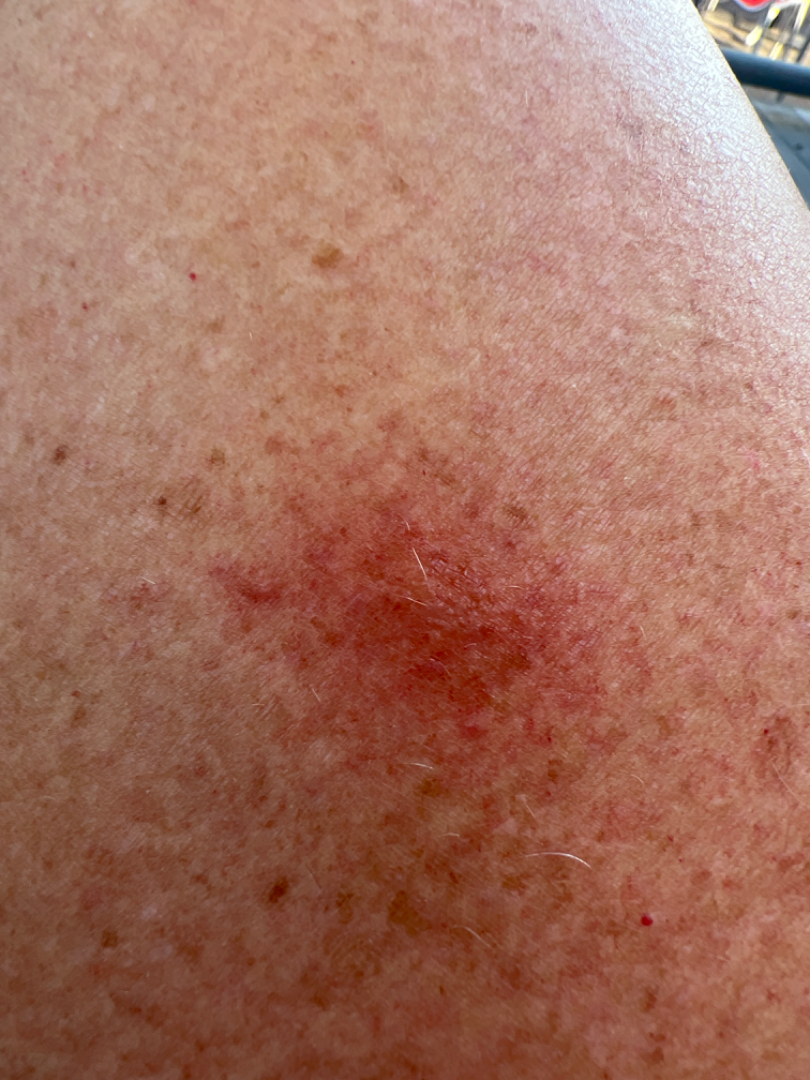| feature | finding |
|---|---|
| assessment | indeterminate from the photograph |
| body site | leg |
| photo taken | close-up |
| texture | fluid-filled and raised or bumpy |
| reported symptoms | none reported |
| duration | about one day |